The subject is a male roughly 80 years of age · dermoscopy of a skin lesion.
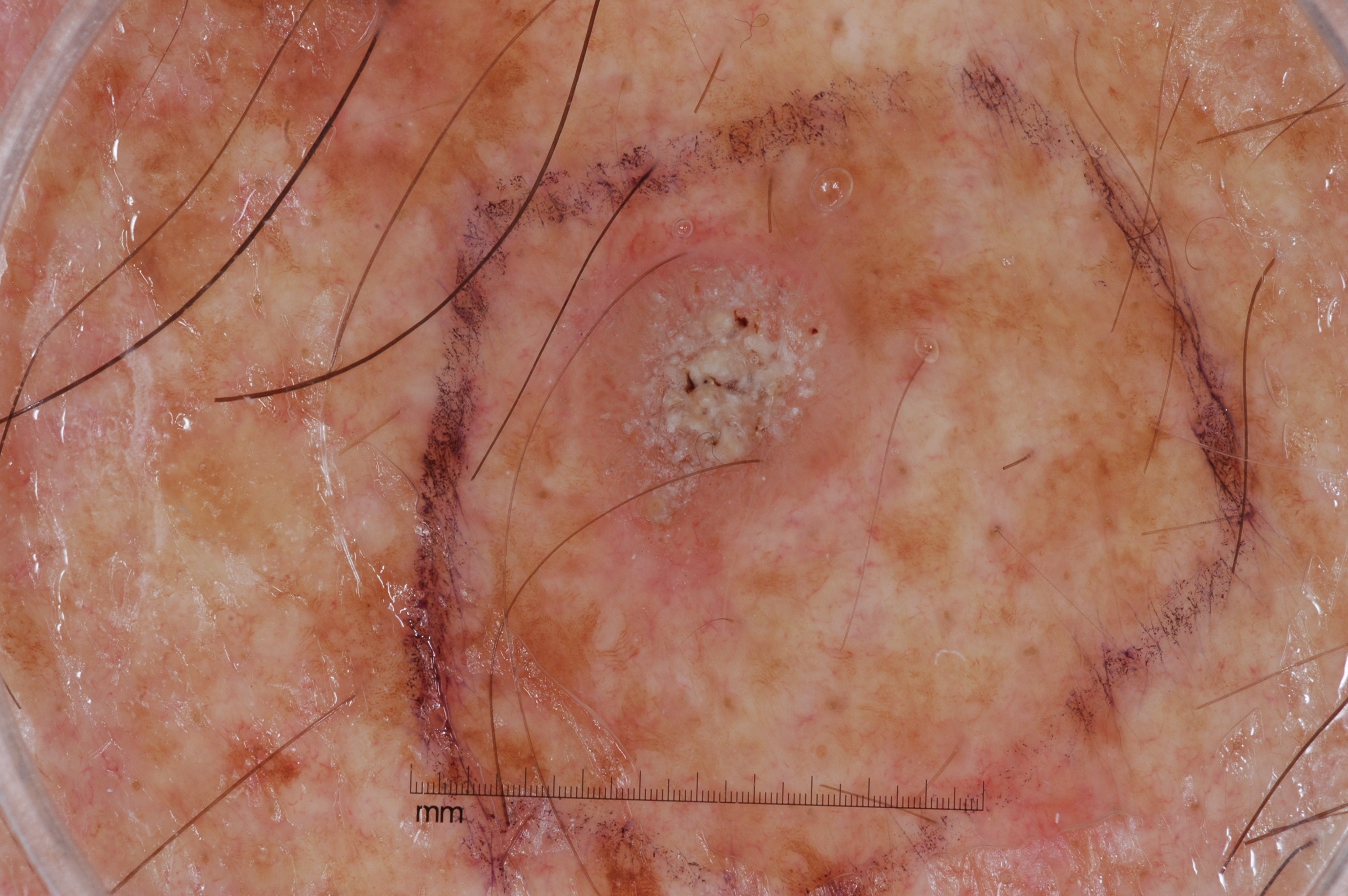Summary: The lesion is small relative to the field of view. With coordinates (x1, y1, x2, y2), lesion location: 560 229 869 598. Dermoscopic review identifies milia-like cysts; no pigment network, negative network, or streaks. Impression: The diagnostic assessment was a seborrheic keratosis.